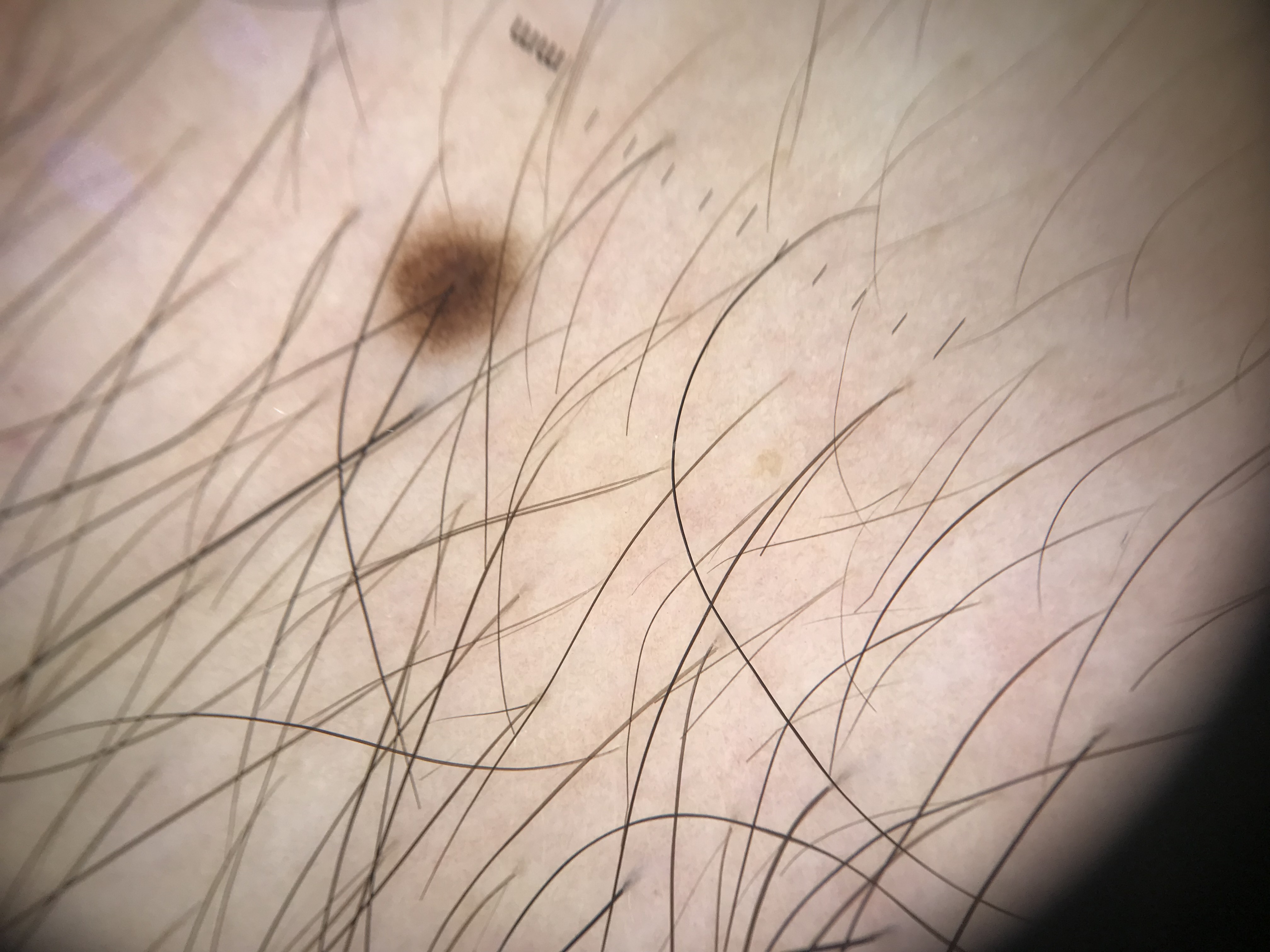image type: dermoscopy
category: banal
label: junctional nevus (expert consensus)